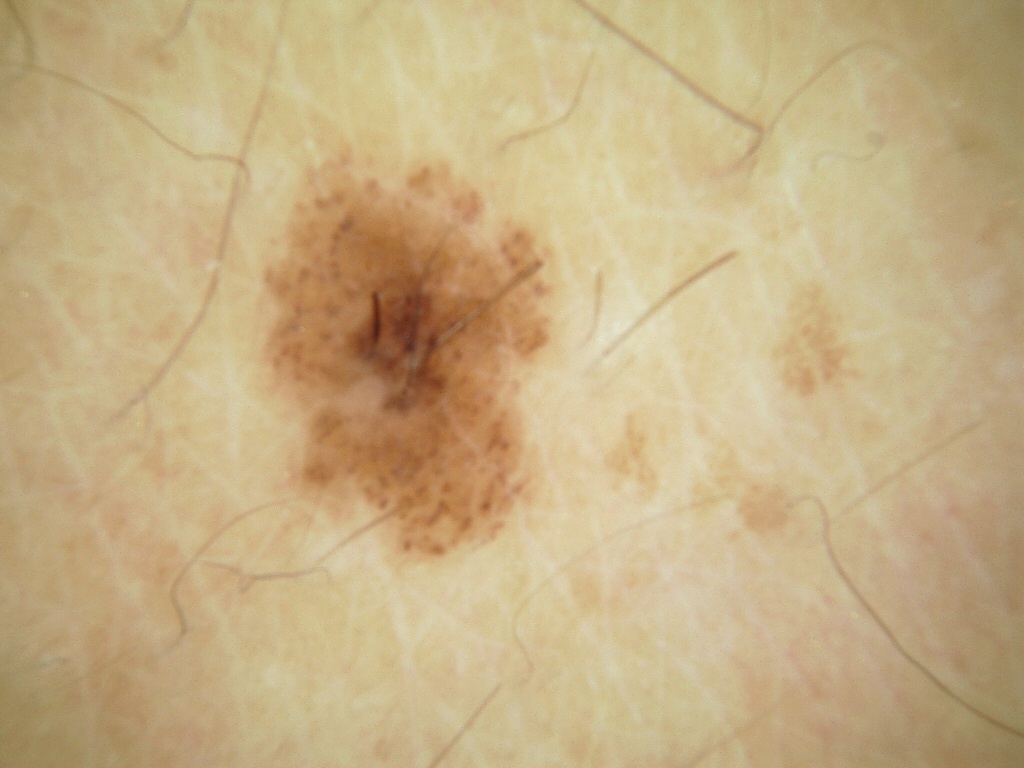A dermoscopic view of a skin lesion.
The lesion is bounded by left=258, top=146, right=550, bottom=559.
Dermoscopic review identifies no globules or streaks.
Diagnosed as a benign skin lesion.